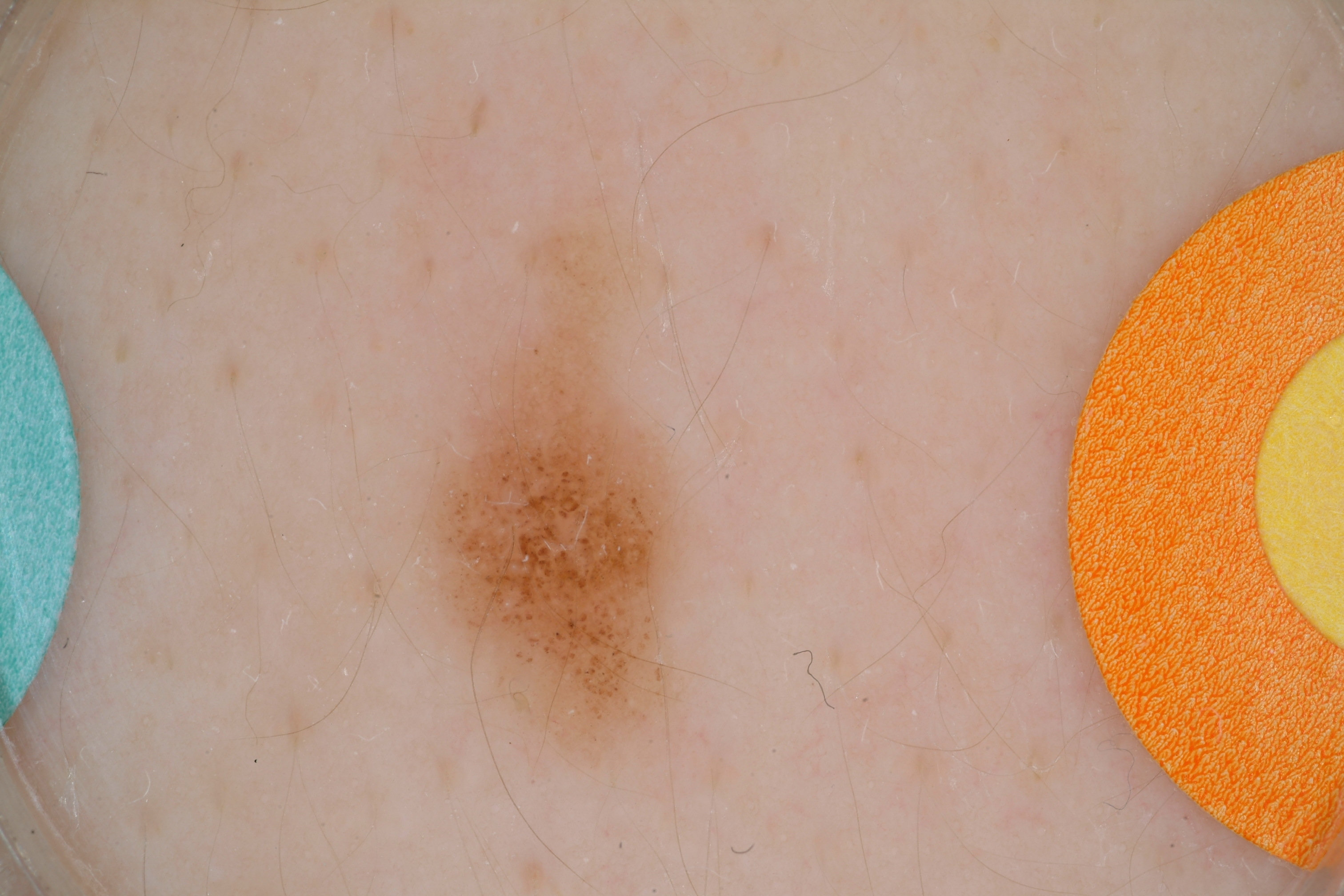- modality · dermoscopic image
- location · <bbox>390, 211, 734, 794</bbox>
- dermoscopic features · globules; absent: milia-like cysts, streaks, pigment network, and negative network
- assessment · a melanocytic nevus